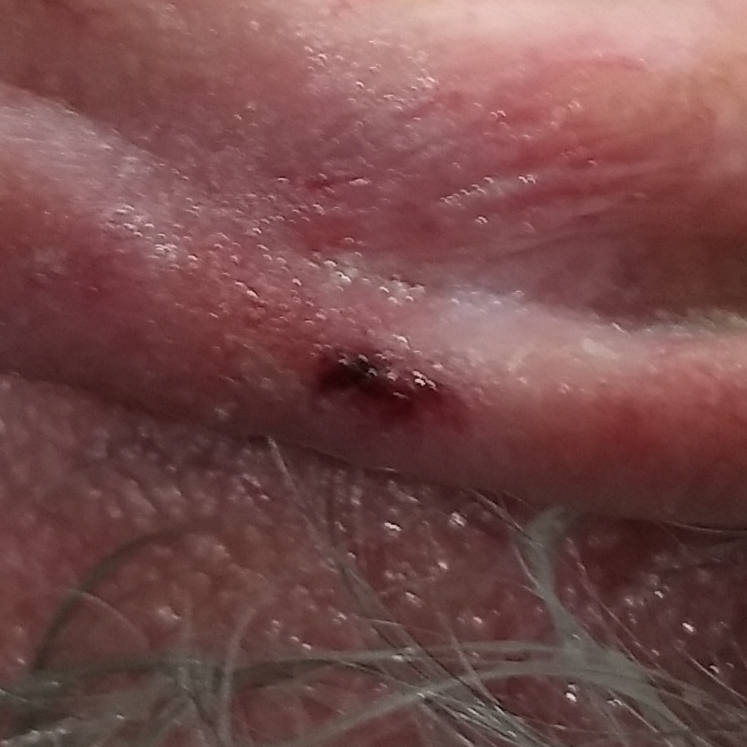Clinical context:
By history, tobacco use, prior malignancy (patient or family), and pesticide exposure. Fitzpatrick skin type II. A male subject 71 years old. A clinical photograph showing a skin lesion. The lesion was found on an ear.
Diagnosis:
Confirmed on histopathology as an actinic keratosis.